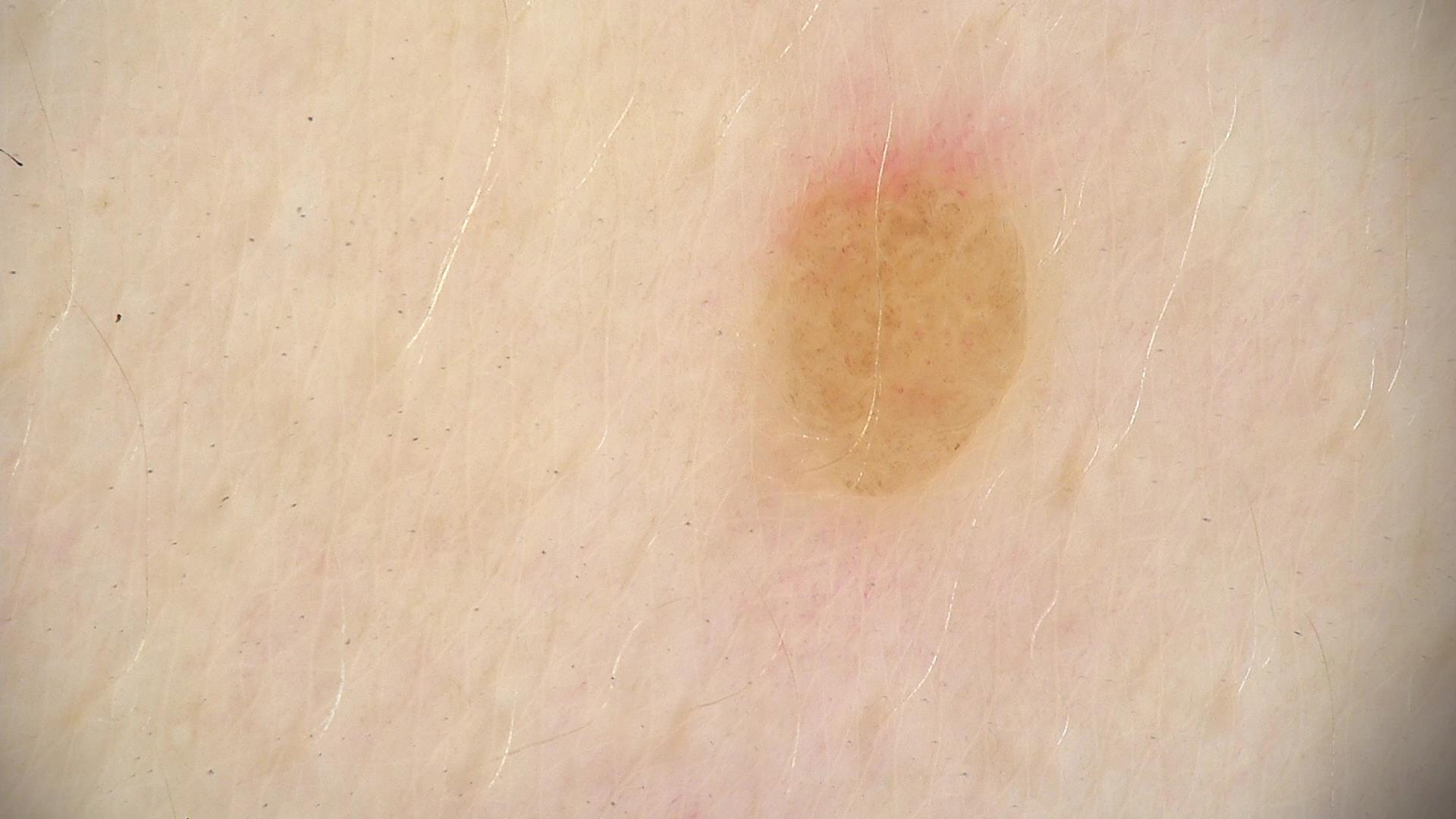{"image": "dermatoscopy", "diagnosis": {"name": "dermal nevus", "code": "db", "malignancy": "benign", "super_class": "melanocytic", "confirmation": "expert consensus"}}